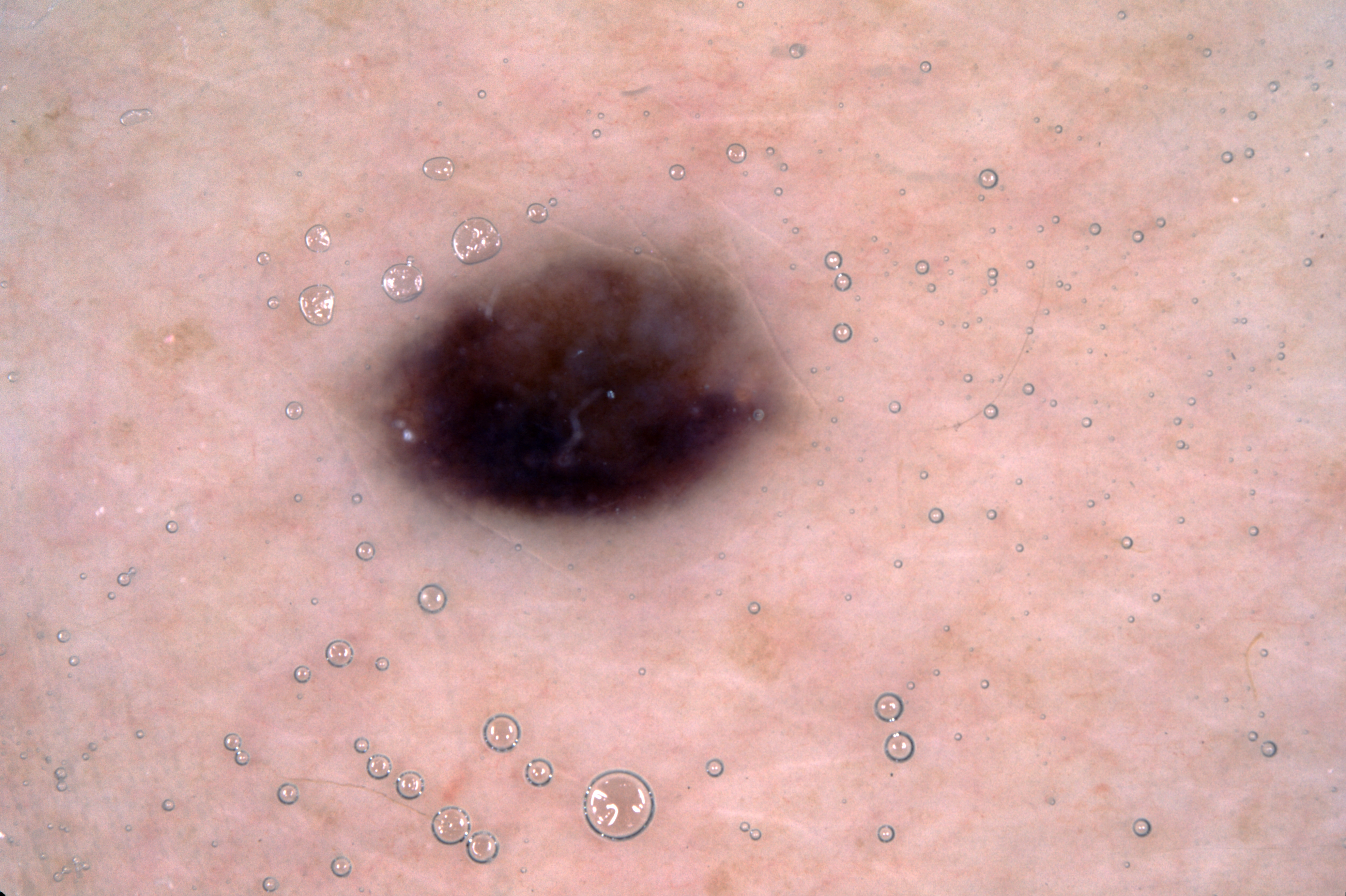subject=female, aged 58-62; image=dermatoscopic image of a skin lesion; absent dermoscopic features=pigment network, milia-like cysts, negative network, and streaks; size=~7% of the field; location=368 245 799 525; diagnosis=a melanocytic nevus, a benign lesion.